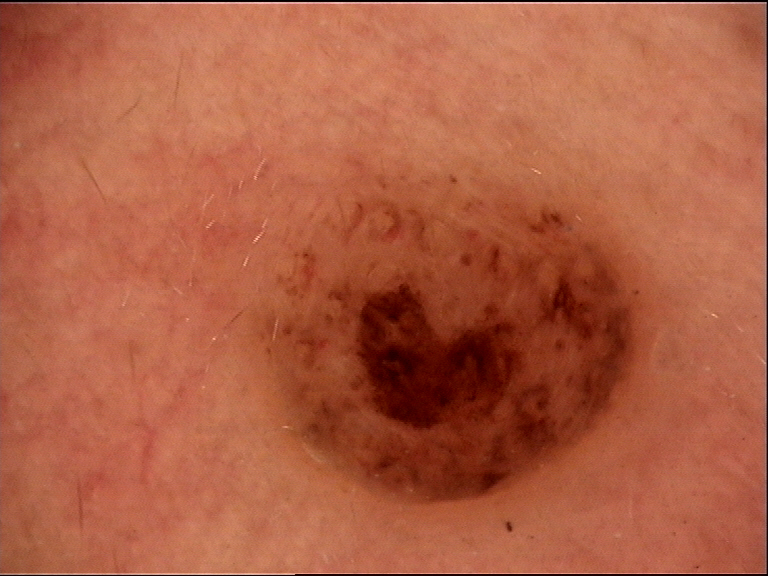assessment=dermal nevus (expert consensus).